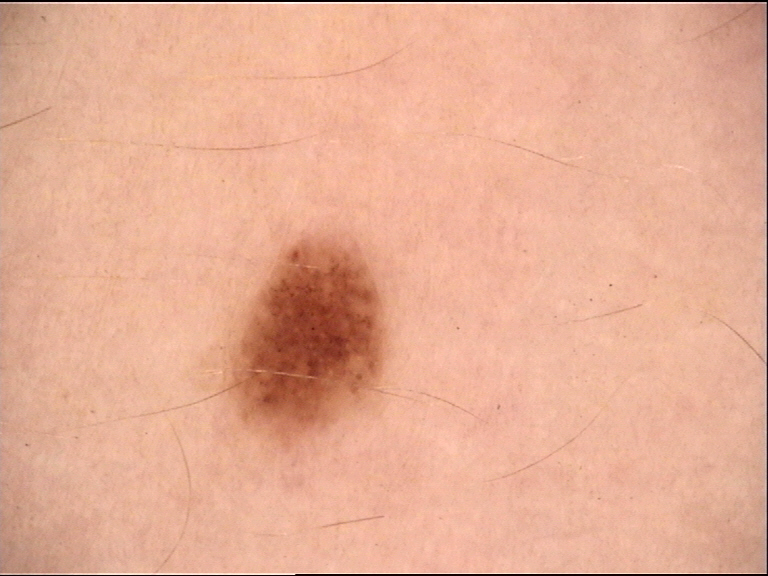– image · dermoscopy
– class · dysplastic junctional nevus (expert consensus)